The contributor reports the lesion is flat, the lesion involves the leg, a close-up photograph:
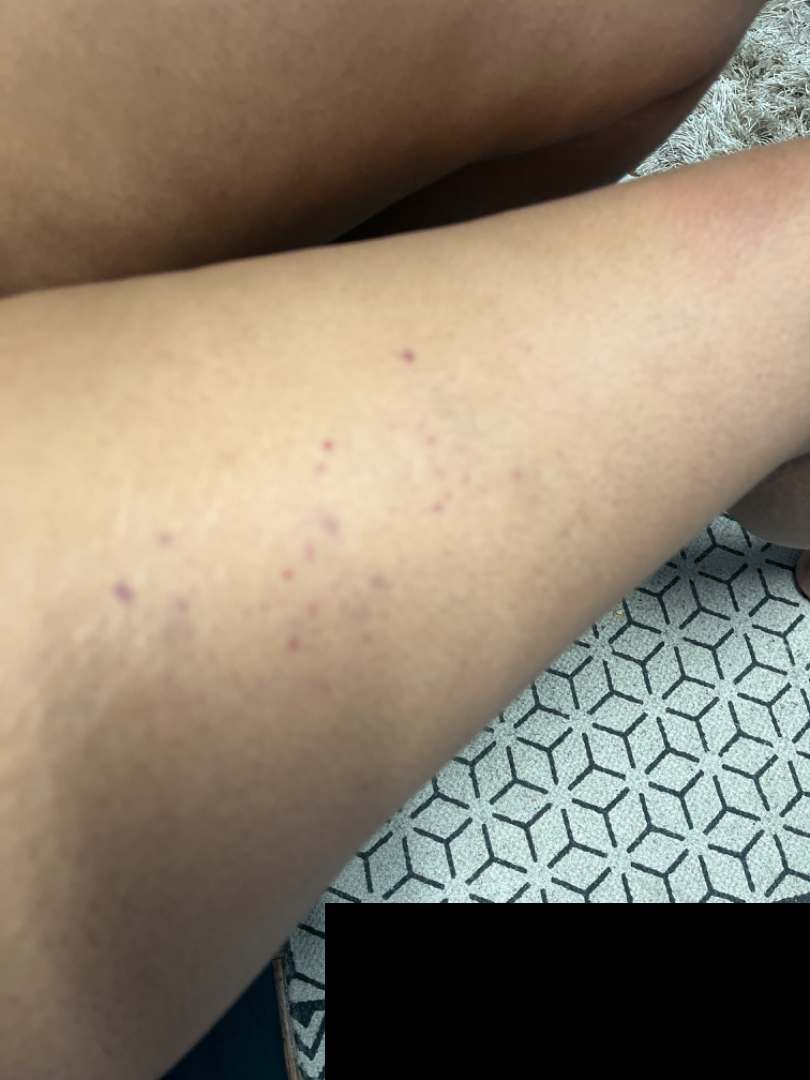The reviewer was unable to grade this case for skin condition.